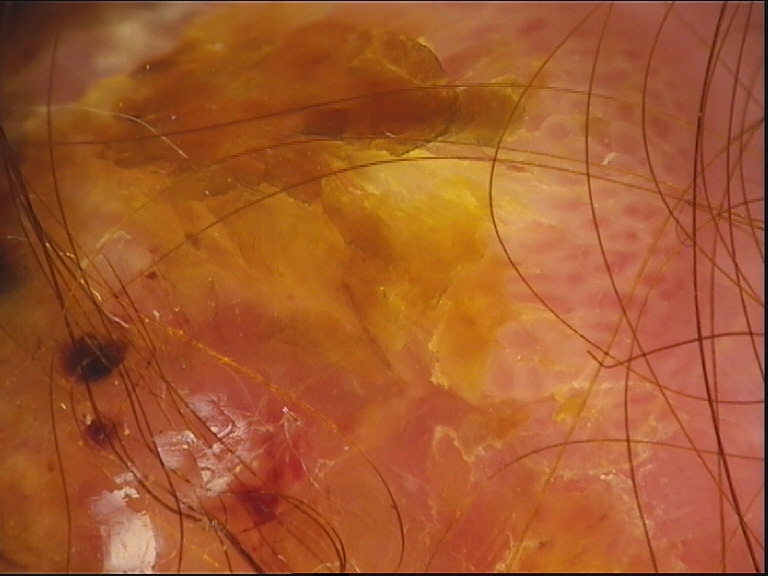Q: What did the workup show?
A: squamous cell carcinoma (biopsy-proven)